A dermoscopic close-up of a skin lesion: 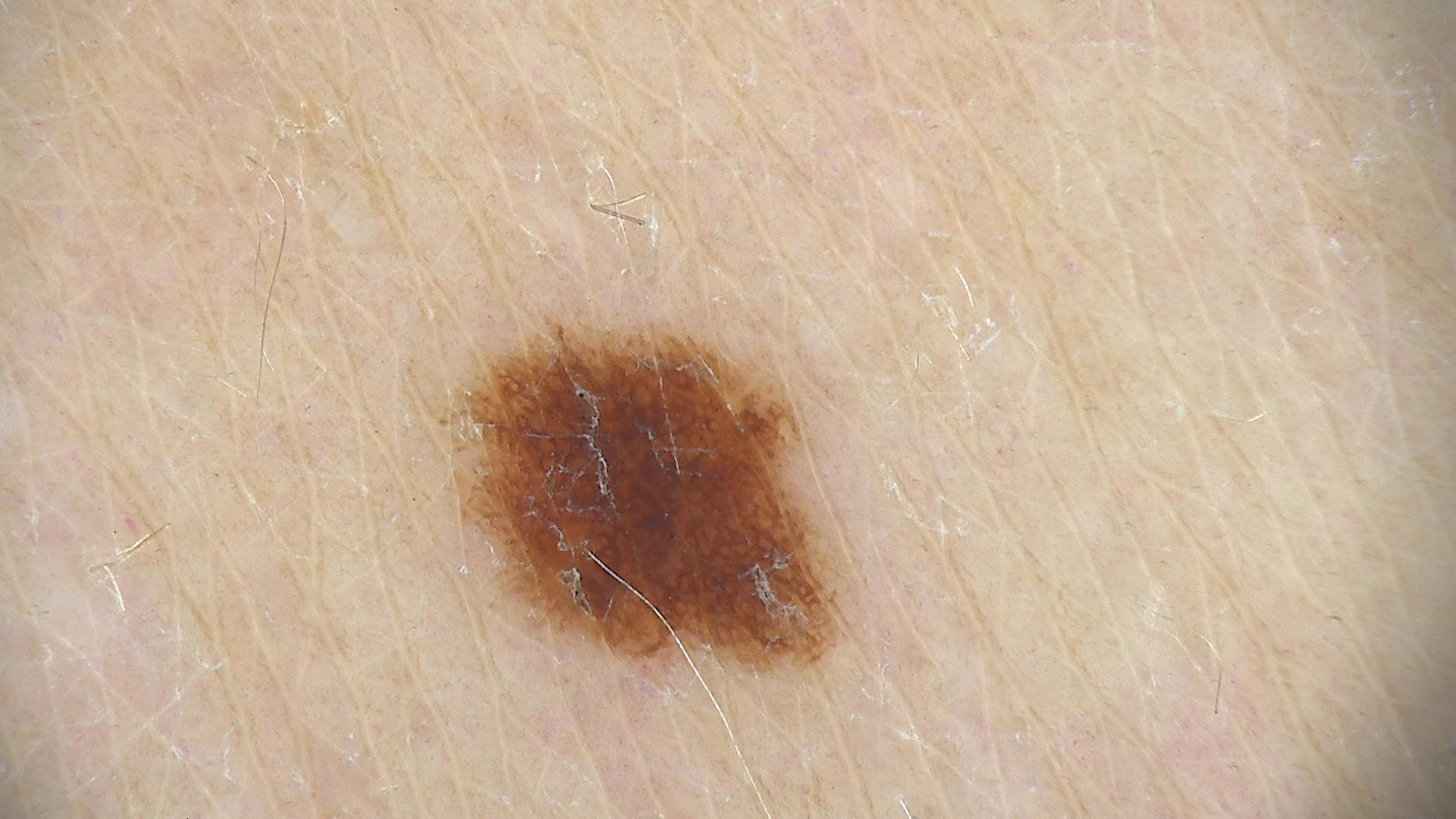| field | value |
|---|---|
| class | dysplastic junctional nevus (expert consensus) |